The photograph is a close-up of the affected area — 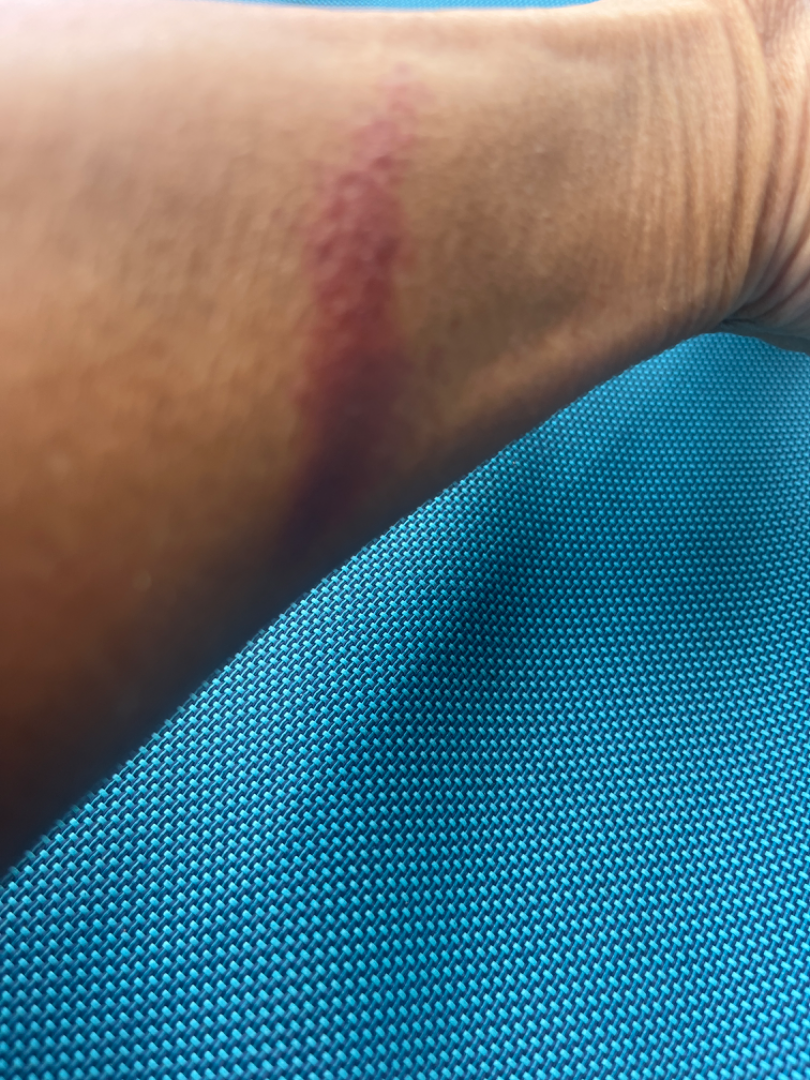Findings:
The image was not sufficient for the reviewer to characterize the skin condition.